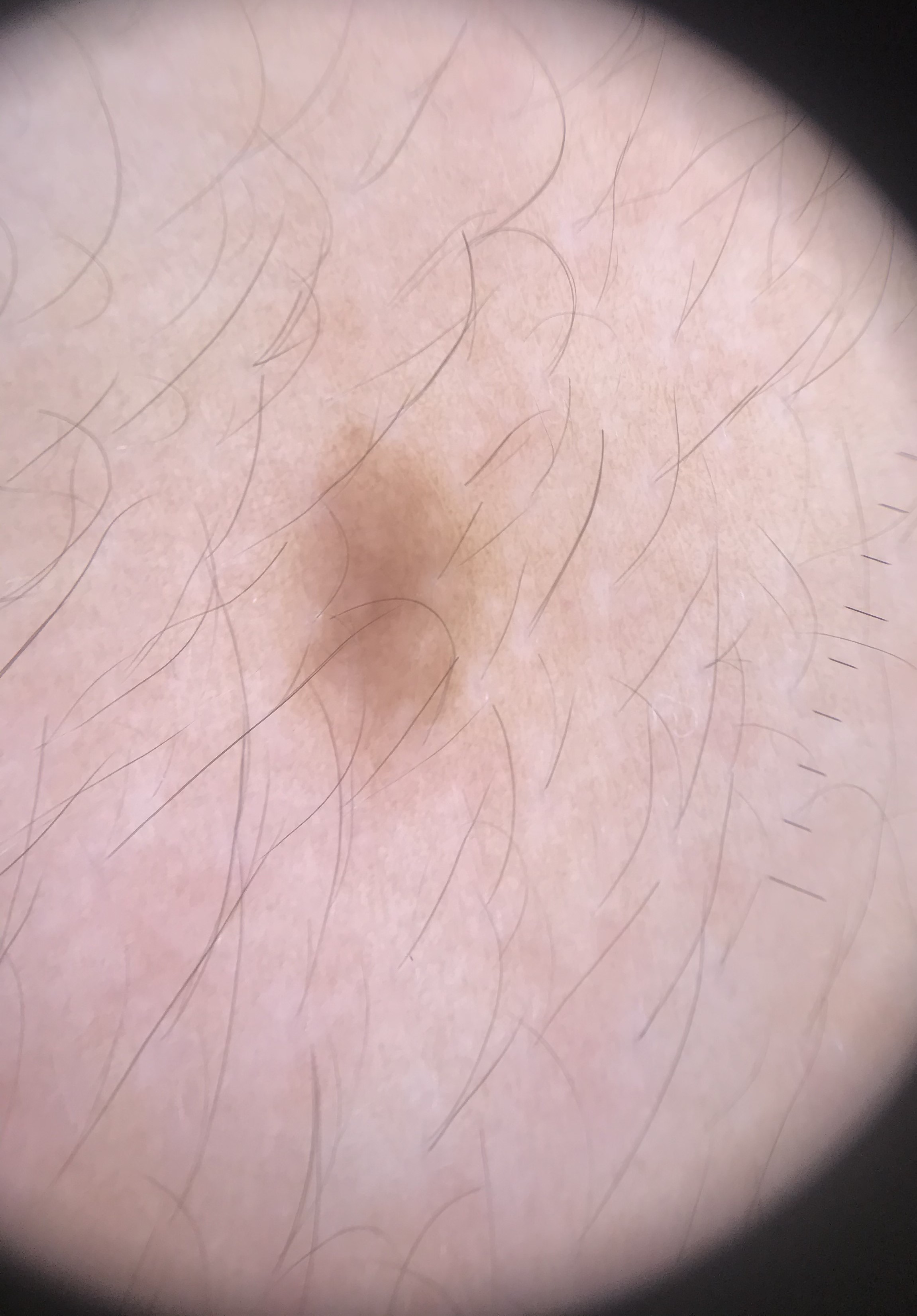{
  "image": "dermatoscopy",
  "diagnosis": {
    "name": "junctional nevus",
    "code": "jb",
    "malignancy": "benign",
    "super_class": "melanocytic",
    "confirmation": "expert consensus"
  }
}